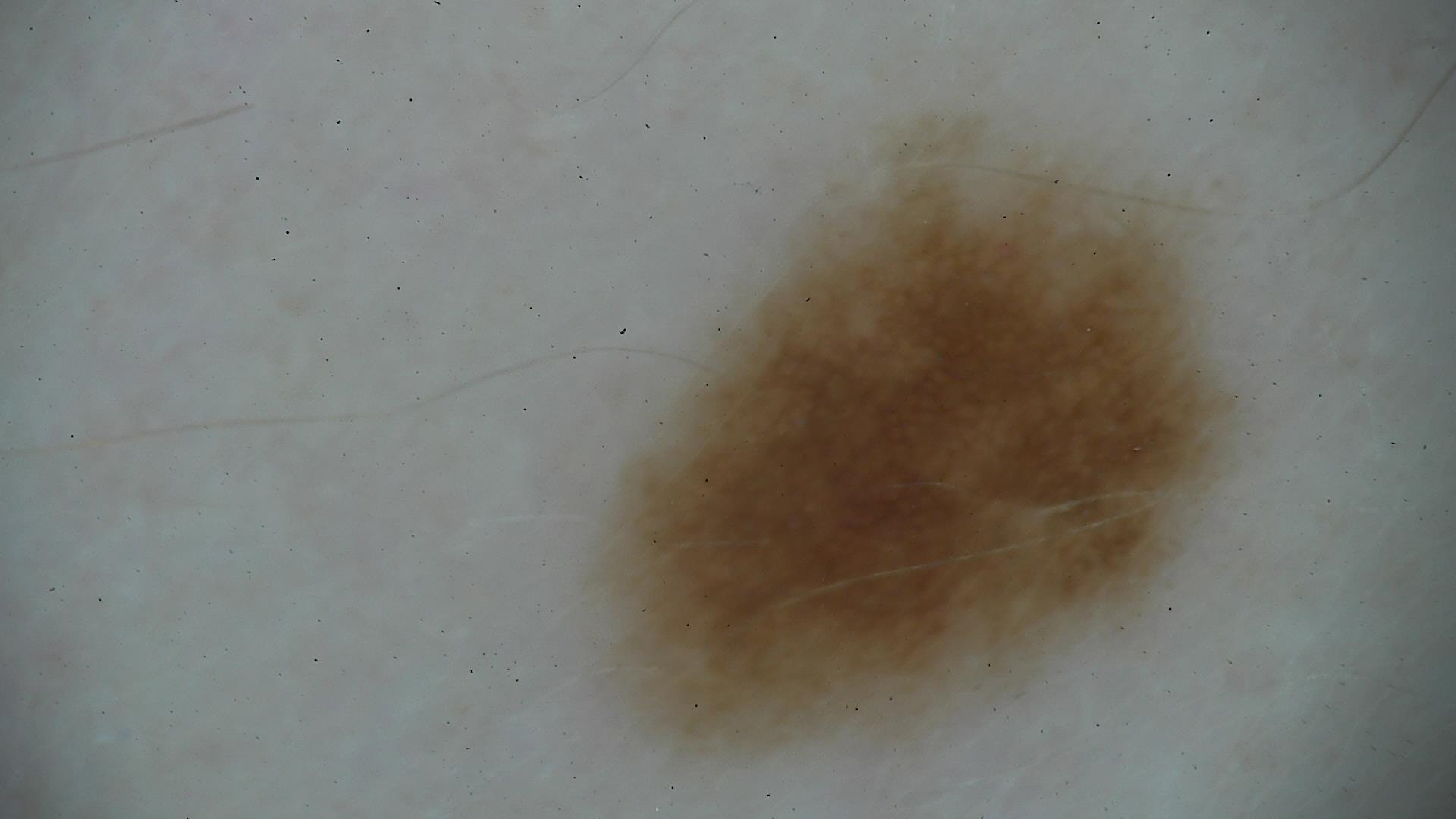A dermoscopic image of a skin lesion.
Labeled as a dysplastic junctional nevus.